An image taken at an angle. The affected area is the leg. The subject is 50–59, female — 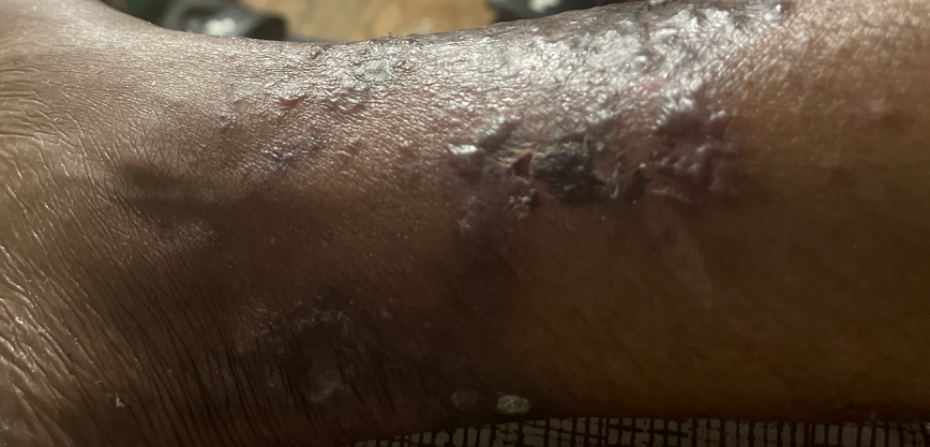dermatologist impression = Eczema (favored); Stasis Dermatitis (possible); Lichen Simplex Chronicus (lower probability); Lichen planus/lichenoid eruption (lower probability)